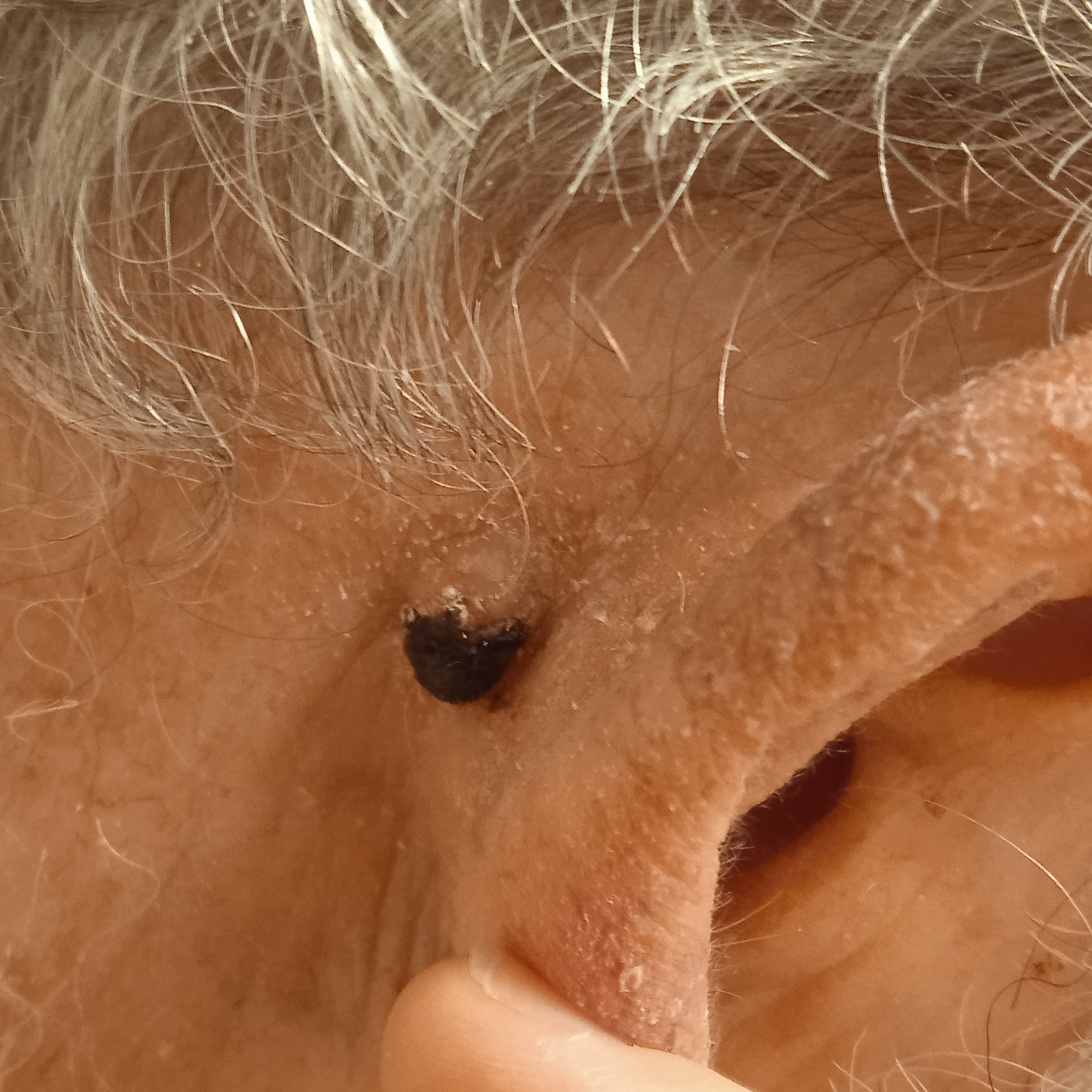Findings:
The referring clinician suspected basal cell carcinoma. The patient reports no prior organ transplant and no family history of skin cancer. A clinical photograph of a skin lesion. The patient says their skin reddens with sun exposure. A male patient 83 years of age. The lesion is located on the head. Measuring roughly 8 mm.
Conclusion:
Histopathologically confirmed as a basal cell carcinoma, following excision, with tumor thickness 2.7 mm.